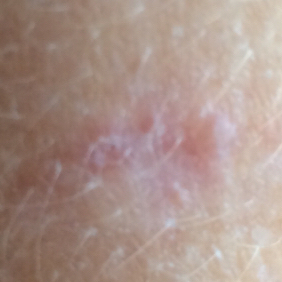patient: female, in their 40s; patient-reported symptoms: growth, itching, elevation; diagnosis: basal cell carcinoma (biopsy-proven).